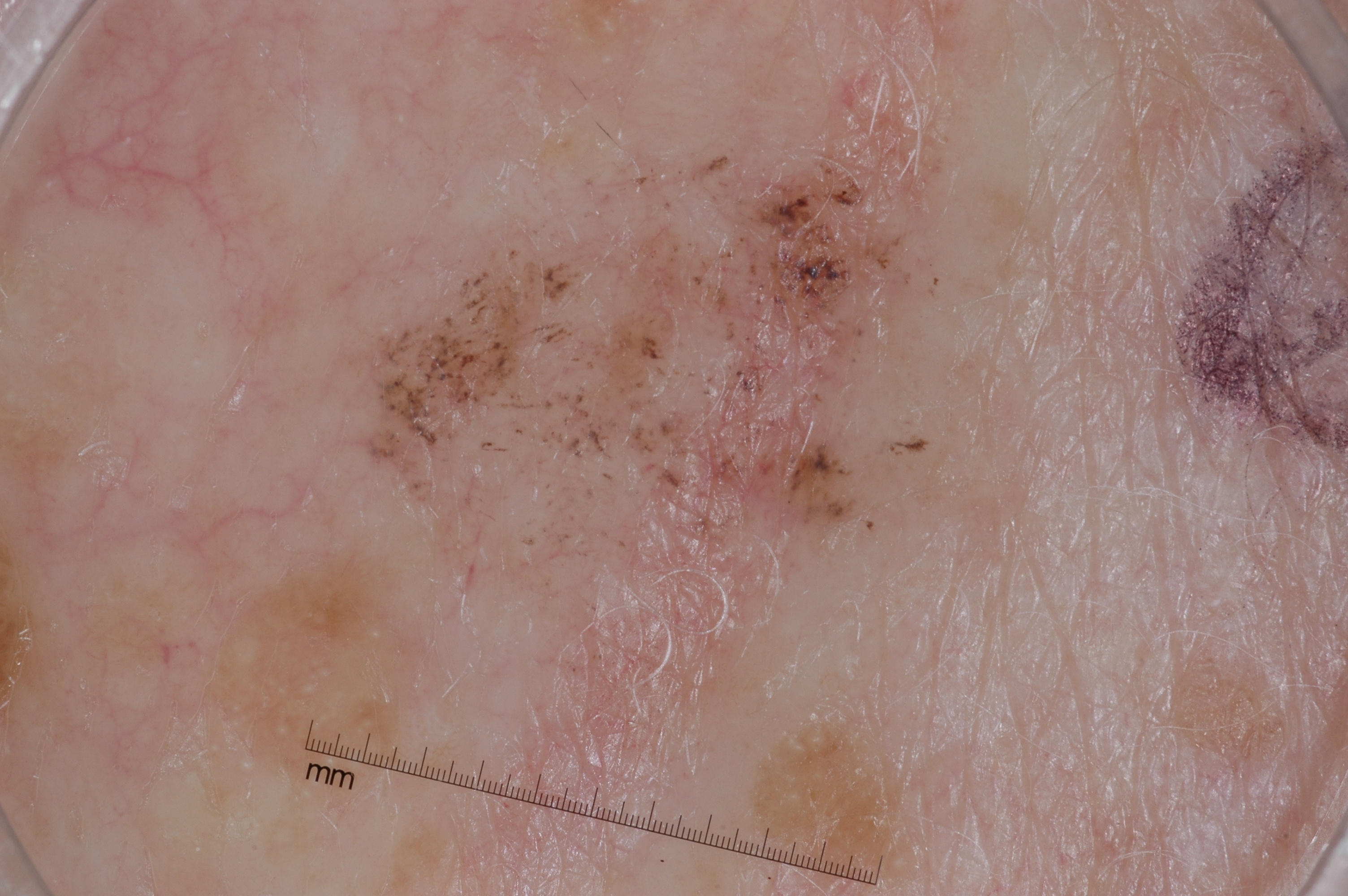Summary: A dermoscopy image of a single skin lesion. A female patient aged approximately 85 or older. The lesion occupies the region left=350, top=71, right=966, bottom=889. The lesion covers approximately 25% of the dermoscopic field. The dermoscopic pattern shows no pigment network, negative network, streaks, or milia-like cysts. Assessment: Consistent with a seborrheic keratosis, a lesion of keratinocytic origin.